This image was taken at an angle; the back of the hand is involved:
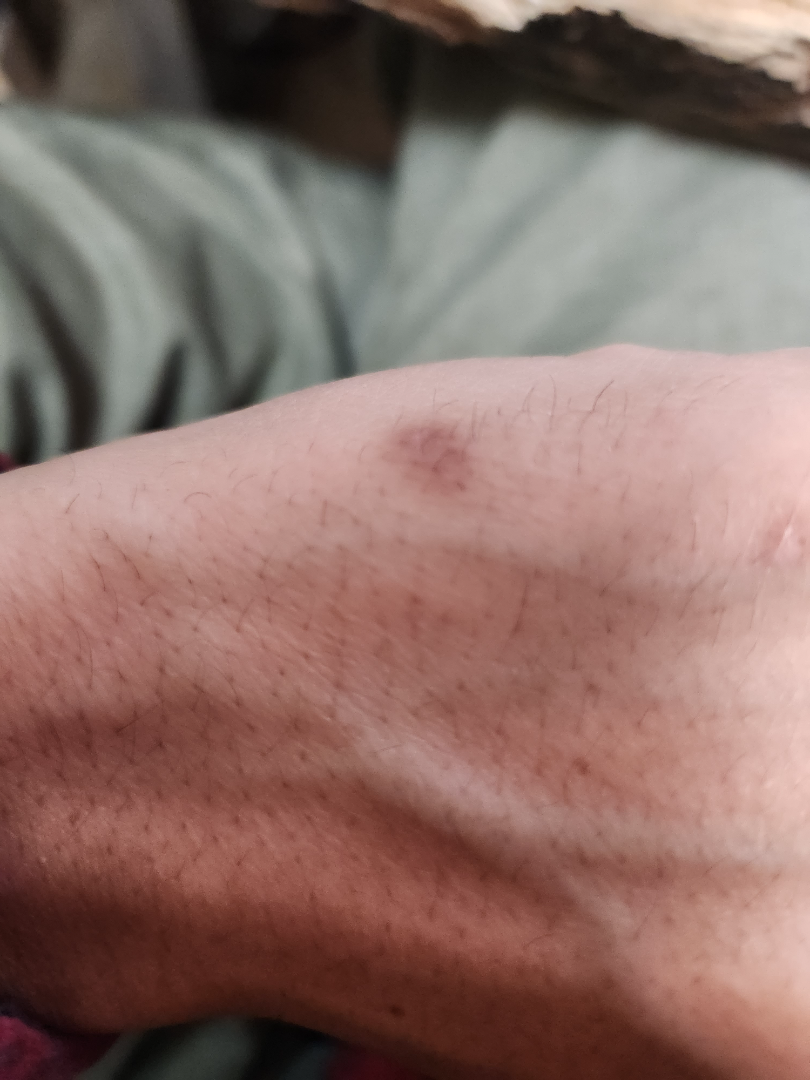differential diagnosis = most likely Prurigo nodularis; also consider Lichen planus/lichenoid eruption; with consideration of Post-Inflammatory hyperpigmentation; less probable is Eczema.